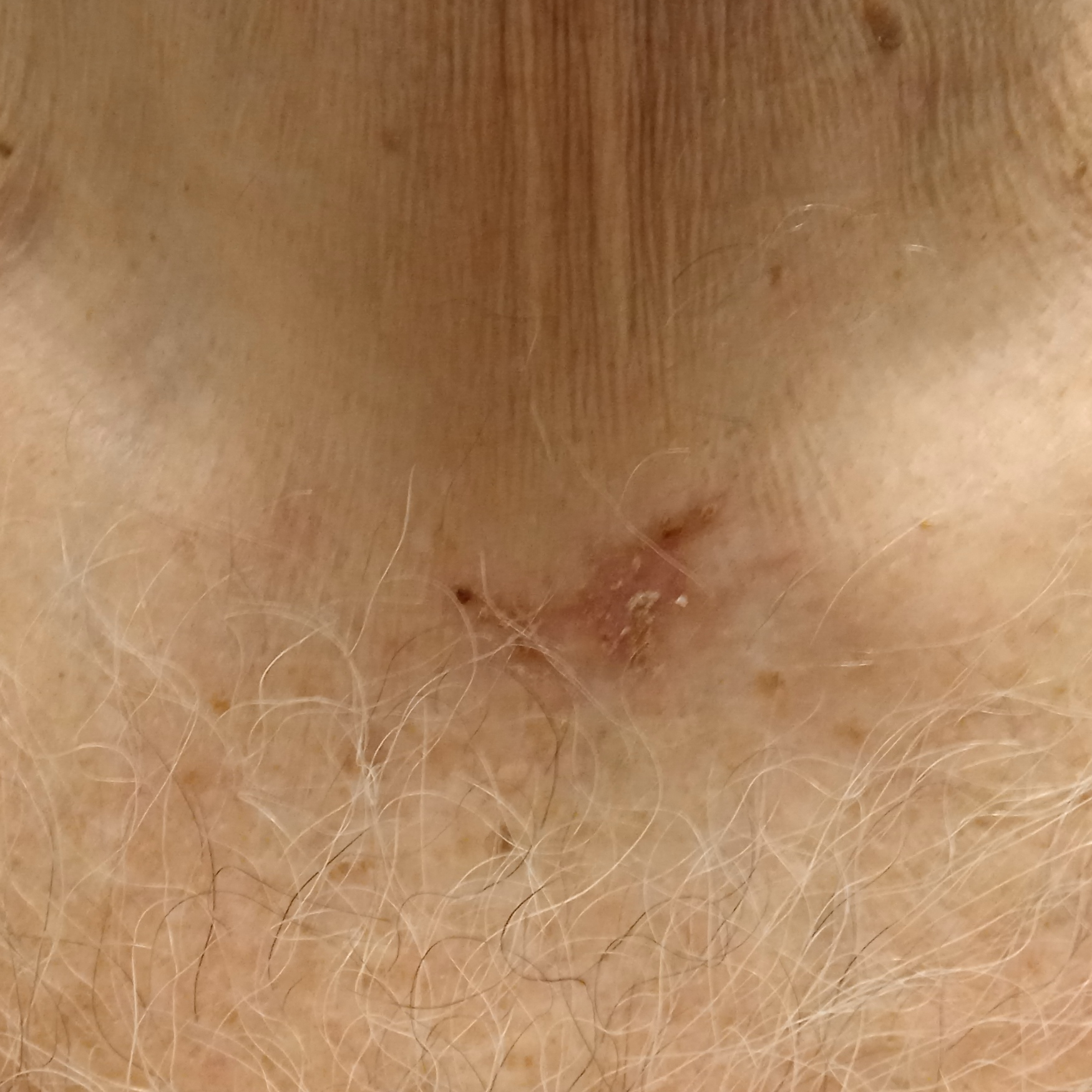Clinical context: Few moles overall by the patient's own estimate. A clinical close-up of a skin lesion. The patient says their skin tans without first burning. Referred for assessment of suspected basal cell carcinoma. A male patient 67 years of age. On a questionnaire the patient reported a personal history of skin cancer. The lesion involves the torso. Measuring roughly 19 mm. Conclusion: On biopsy, the diagnosis was a basal cell carcinoma, following a punch biopsy, with tumor thickness 0.8 mm.